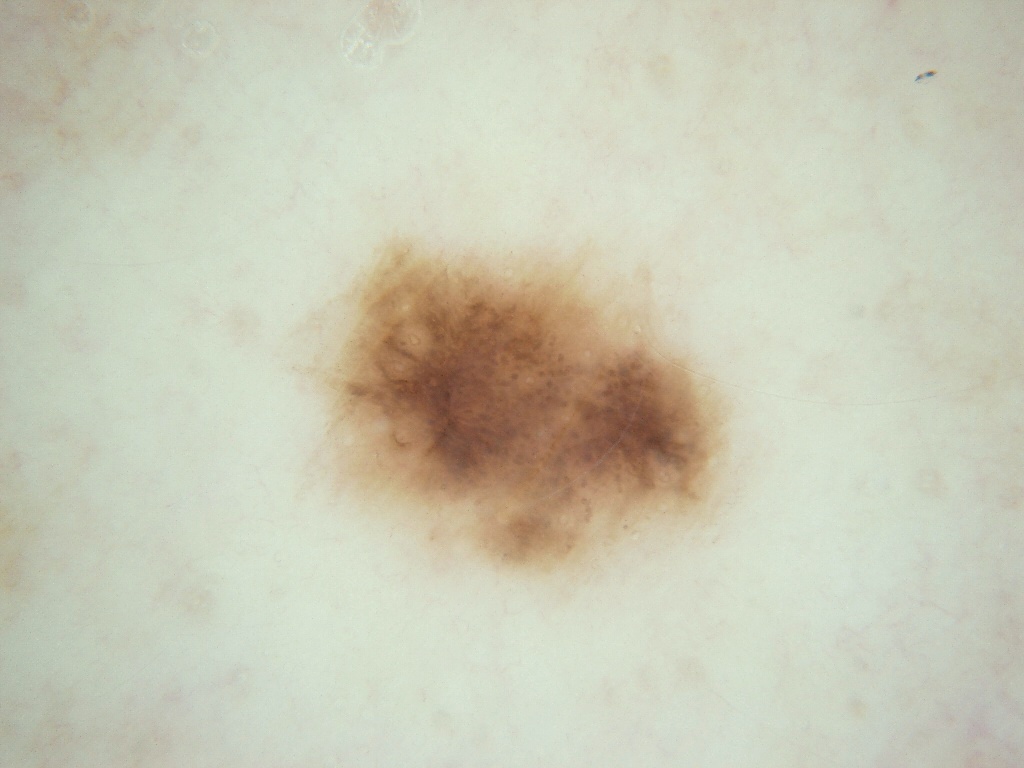Case summary: A dermoscopic close-up of a skin lesion. With coordinates (x1, y1, x2, y2), the lesion spans [311, 236, 726, 573]. Assessment: Consistent with a melanocytic nevus.